Close-up view:
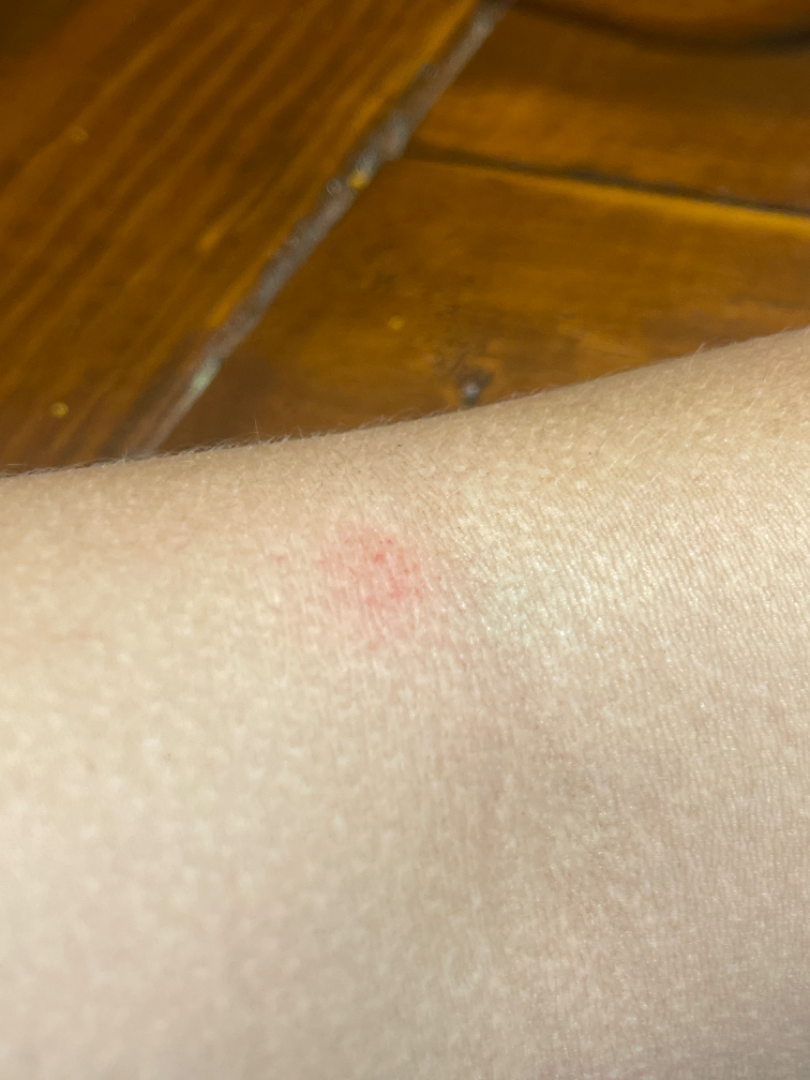Review:
Eczema (favored); Acute dermatitis, NOS (considered).